A female subject age 64 · the patient says their skin tans without first burning · a dermatoscopic image of a skin lesion · by self-report, a personal history of cancer, a family history of skin cancer, no immunosuppression, and no sunbed use · the referring clinician suspected basal cell carcinoma: 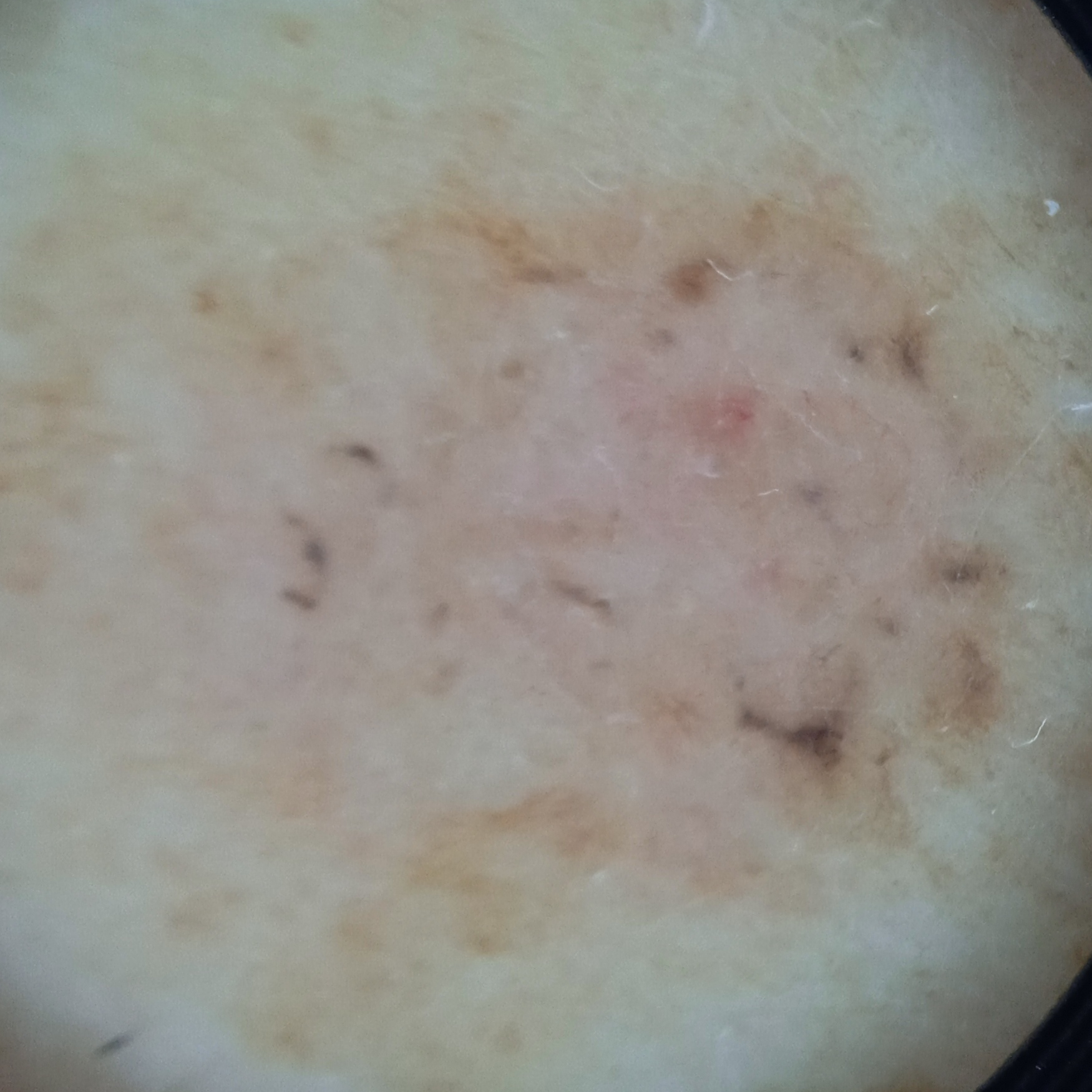* body site: the back
* lesion size: 9.8 mm
* diagnosis: basal cell carcinoma (biopsy-proven)